A dermoscopic close-up of a skin lesion: 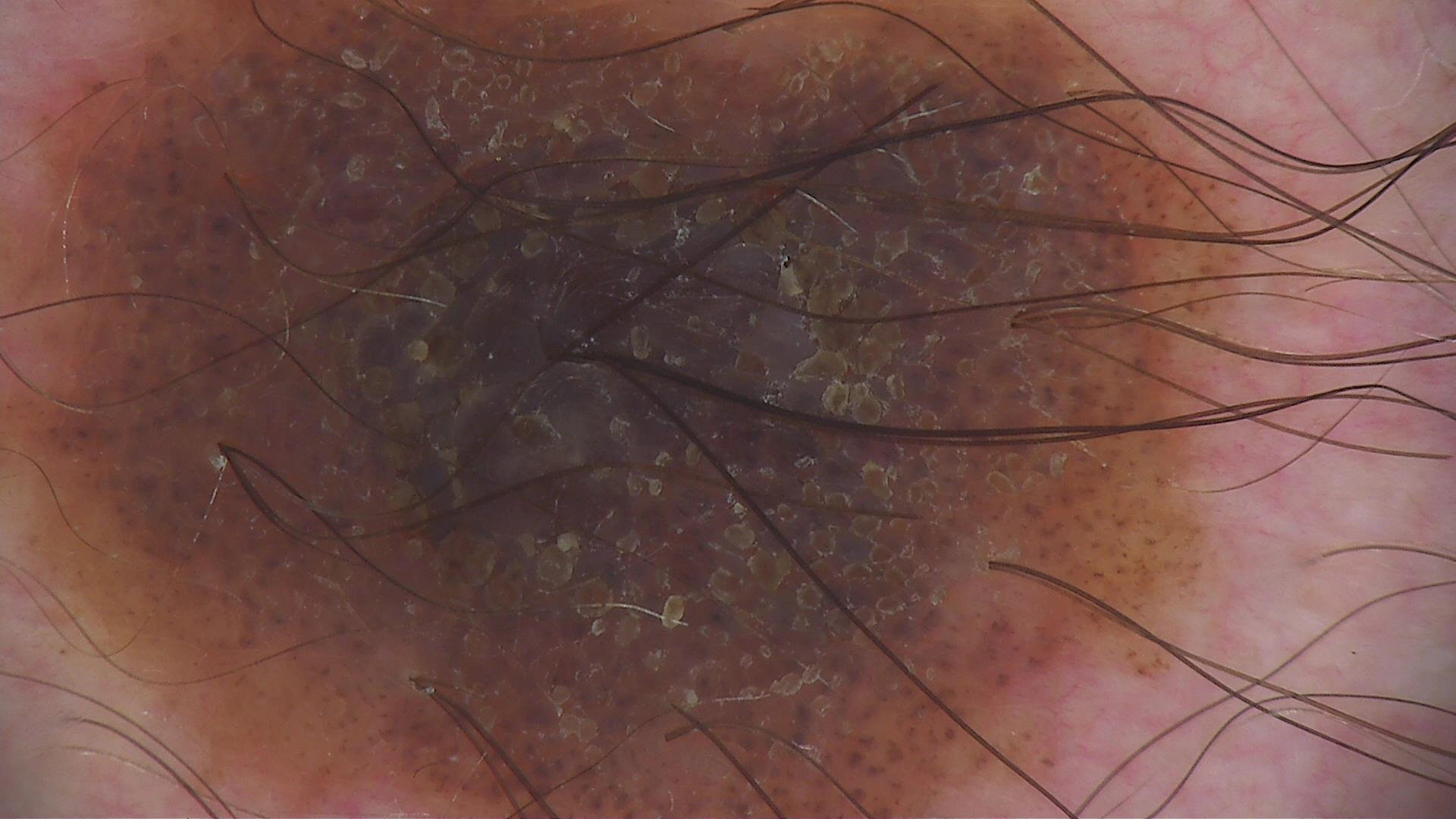Findings:
• assessment — dysplastic compound nevus (expert consensus)